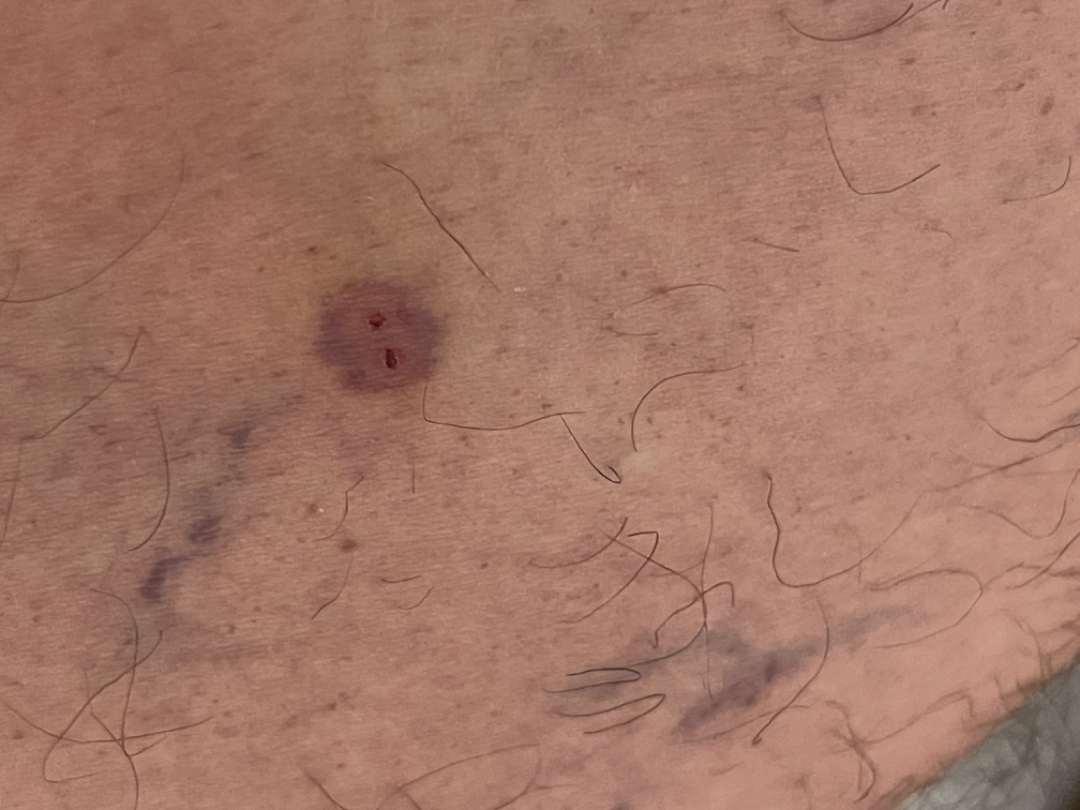  assessment: could not be assessed
  shot_type: at an angle